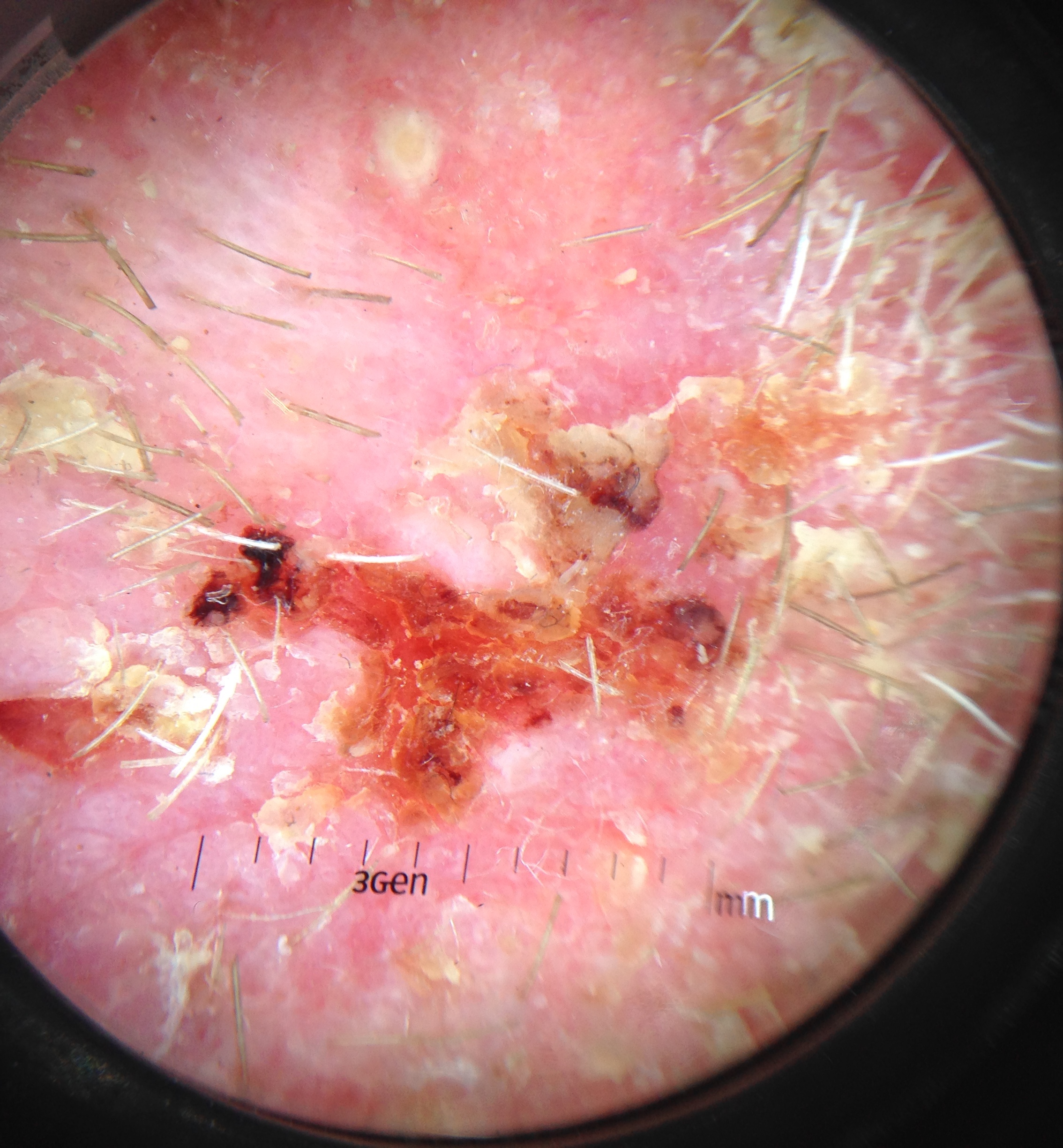Conclusion:
Histopathology confirmed a keratinocytic lesion — a squamous cell carcinoma.